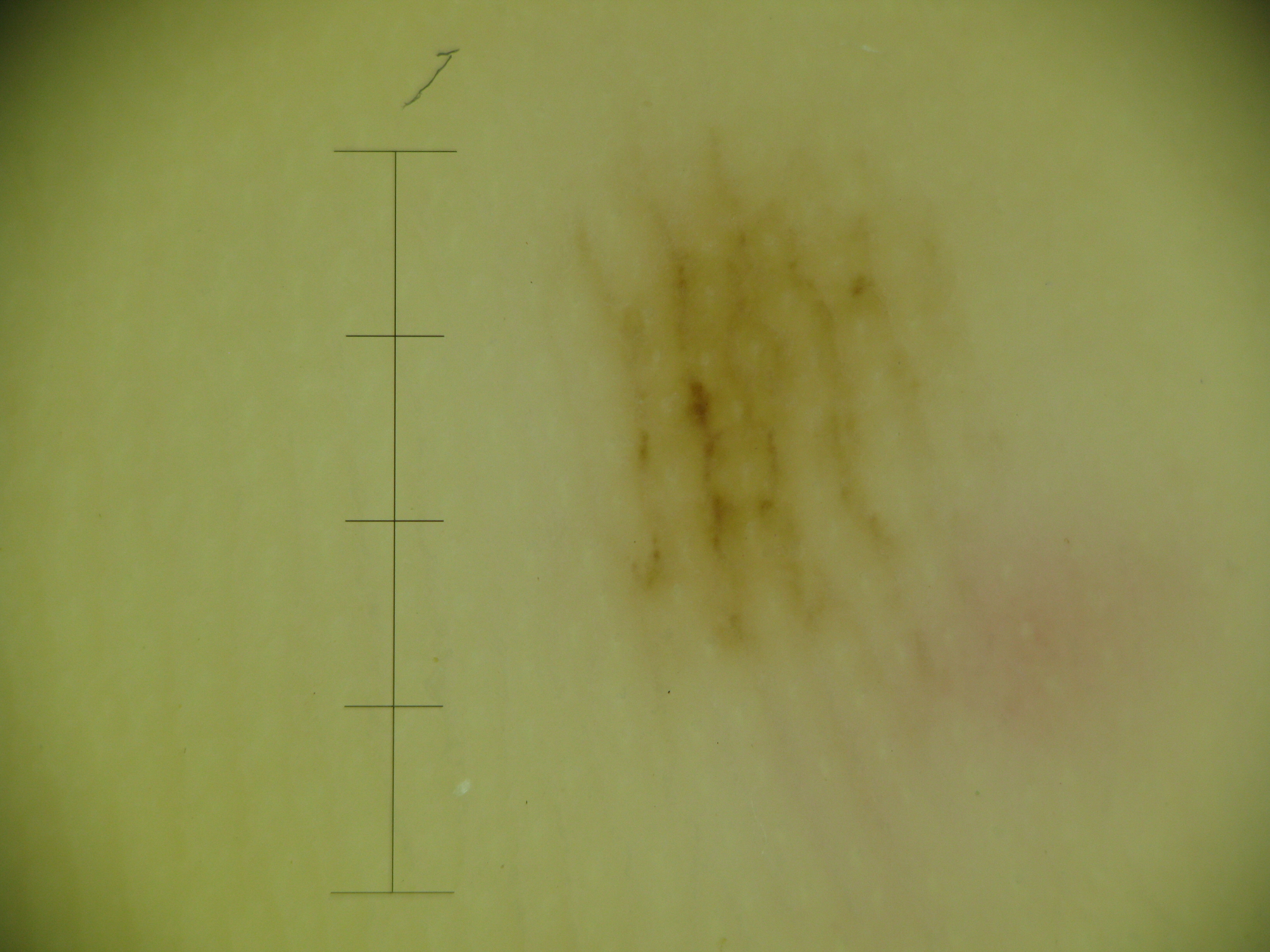<case>
<diagnosis>
<name>acral junctional nevus</name>
<code>ajb</code>
<malignancy>benign</malignancy>
<super_class>melanocytic</super_class>
<confirmation>expert consensus</confirmation>
</diagnosis>
</case>